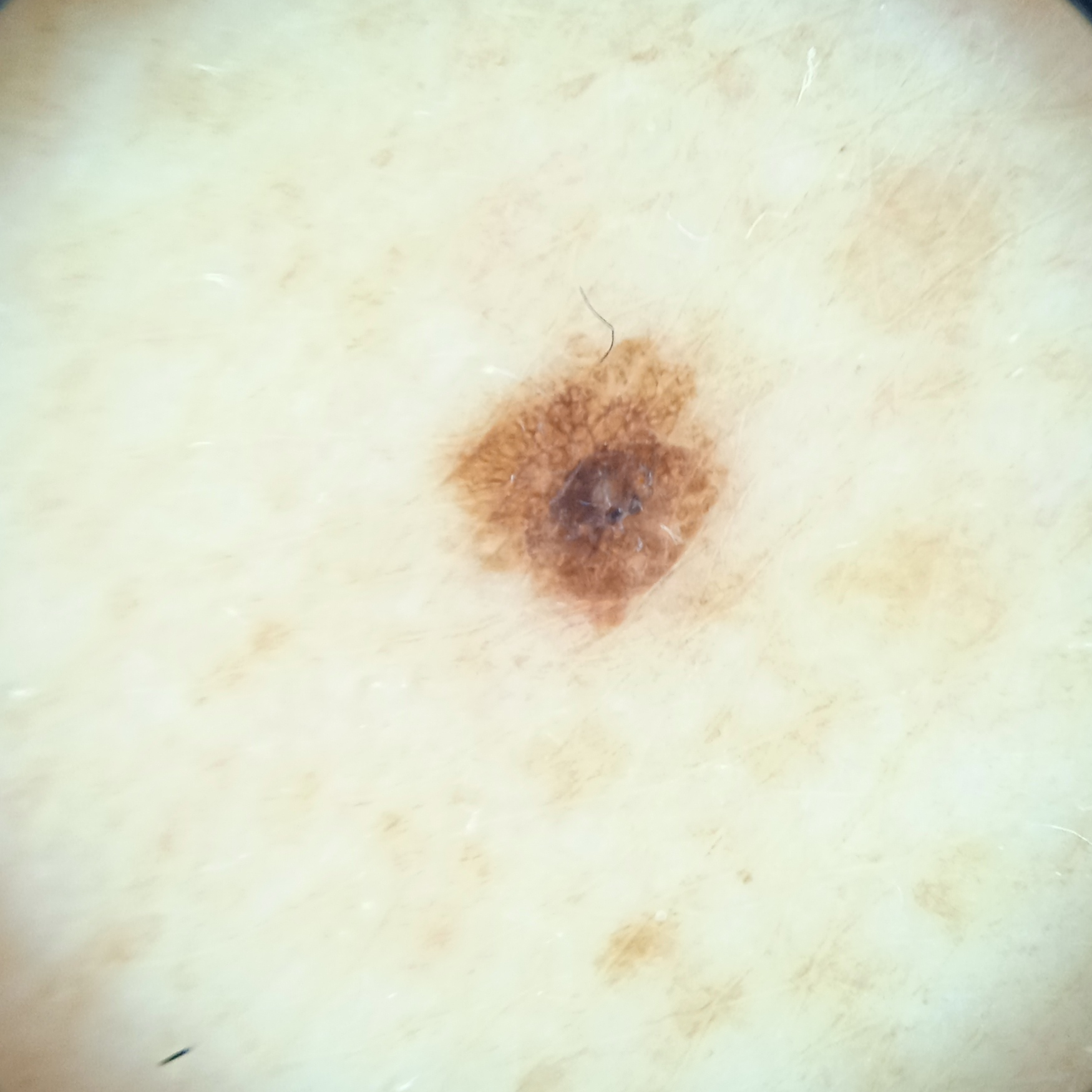Findings: The patient describes having a moderate number of moles. Referred with a clinical suspicion of seborrheic keratosis. Dermoscopy of a skin lesion. On a questionnaire the patient reported a family history of skin cancer and a personal history of cancer. The lesion is located on the back. Measuring roughly 3.5 mm. Diagnosis: Histopathologically confirmed as a seborrheic keratosis, following excision.